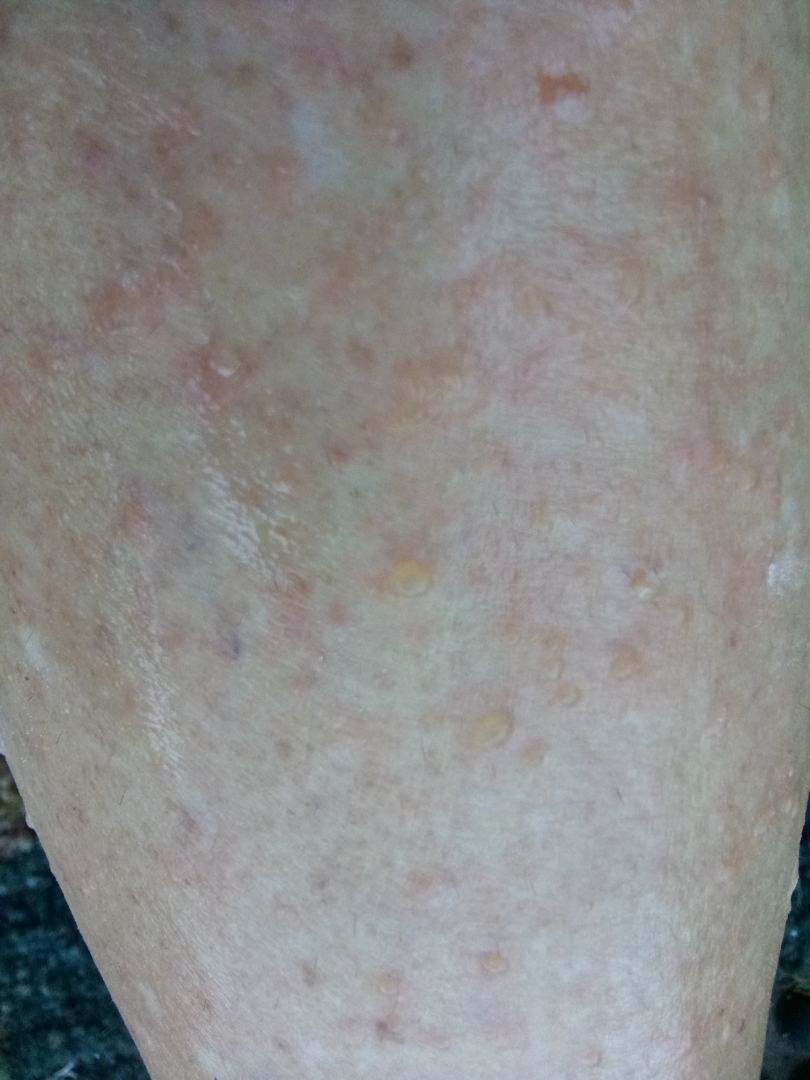This image was taken at an angle.
Symptoms reported: pain, itching and burning.
Texture is reported as raised or bumpy and fluid-filled.
The lesion involves the arm and leg.
The condition has been present for less than one week.
The patient notes associated fatigue.
Skin tone: Fitzpatrick skin type III.
Self-categorized by the patient as a rash.
On remote dermatologist review: most consistent with Stasis Dermatitis.